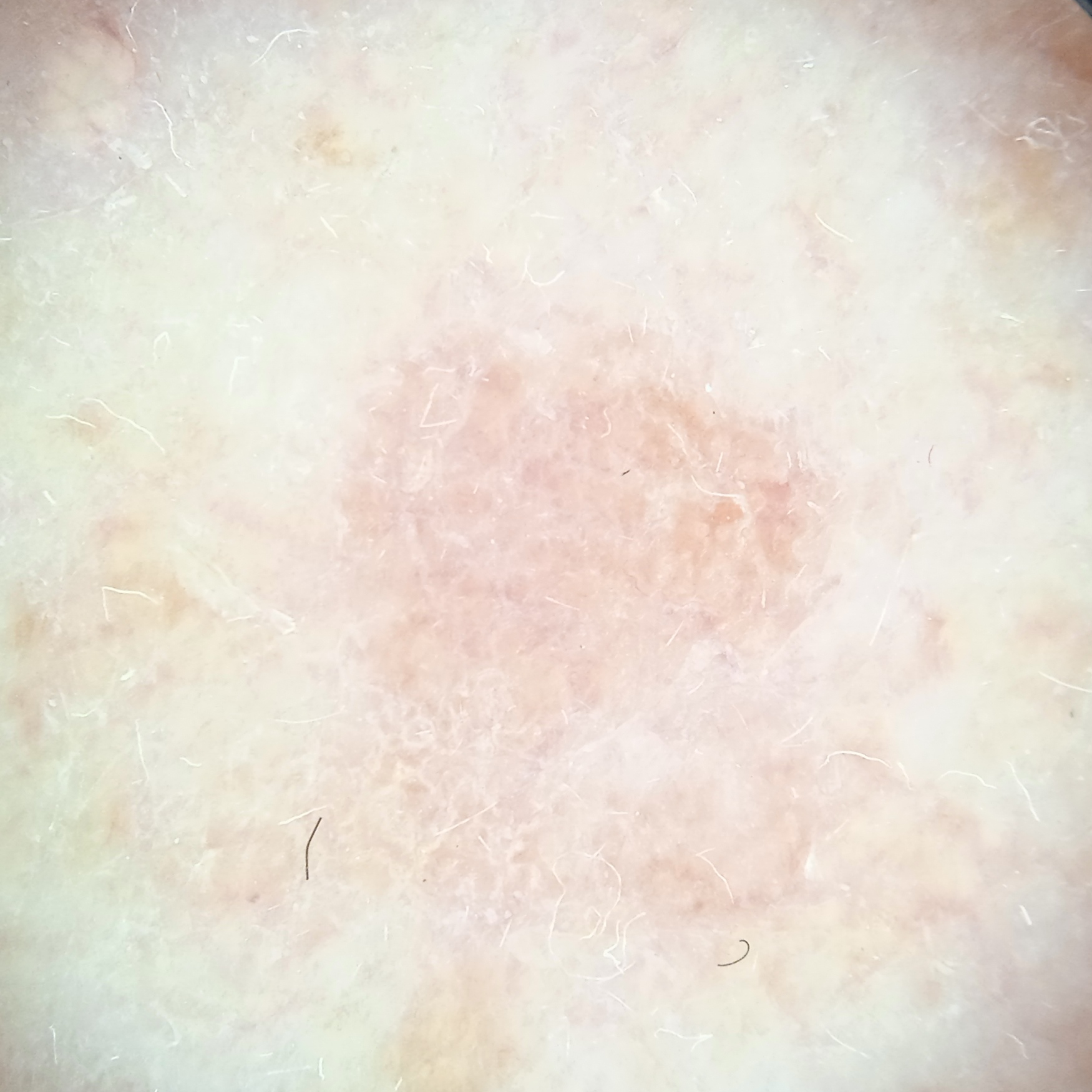- image — dermoscopy
- referral — clinical suspicion of basal cell carcinoma
- subject — female, age 55
- nevus count — a moderate number of melanocytic nevi
- sun reaction — skin reddens painfully with sun exposure
- relevant history — immunosuppression, a prior organ transplant
- body site — the face
- size — 5.7 mm
- assessment — actinic keratosis (dermatologist consensus)